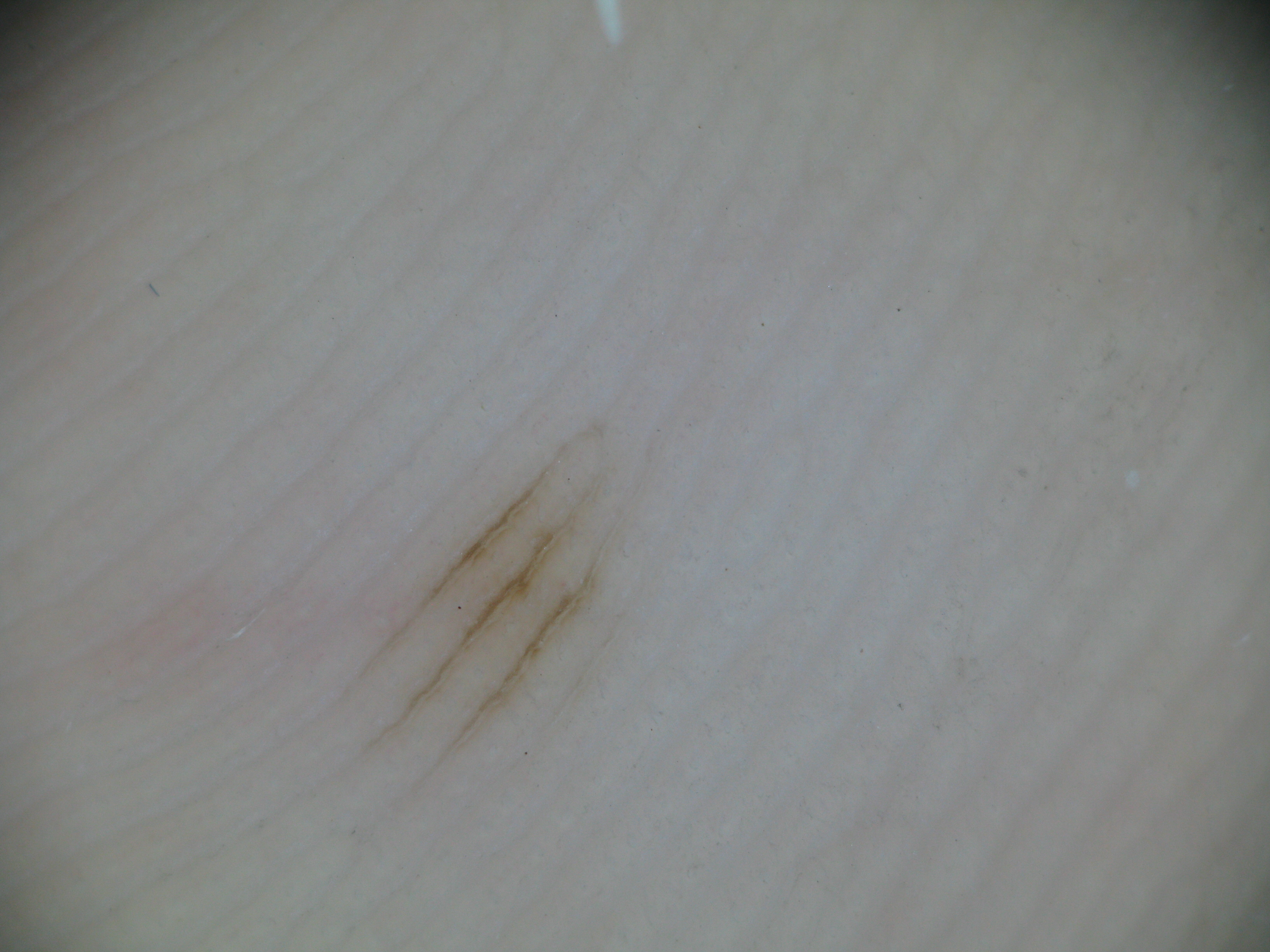Classified as an acral junctional nevus.